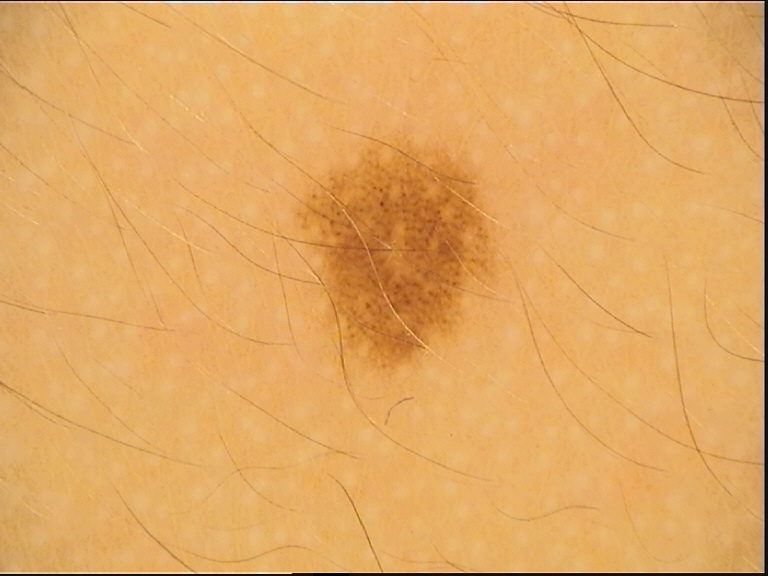Classified as a benign lesion — a dysplastic junctional nevus.